The condition has been present for three to twelve months; reported lesion symptoms include itching; self-categorized by the patient as a rash; no associated systemic symptoms reported; the photo was captured at an angle; located on the arm: 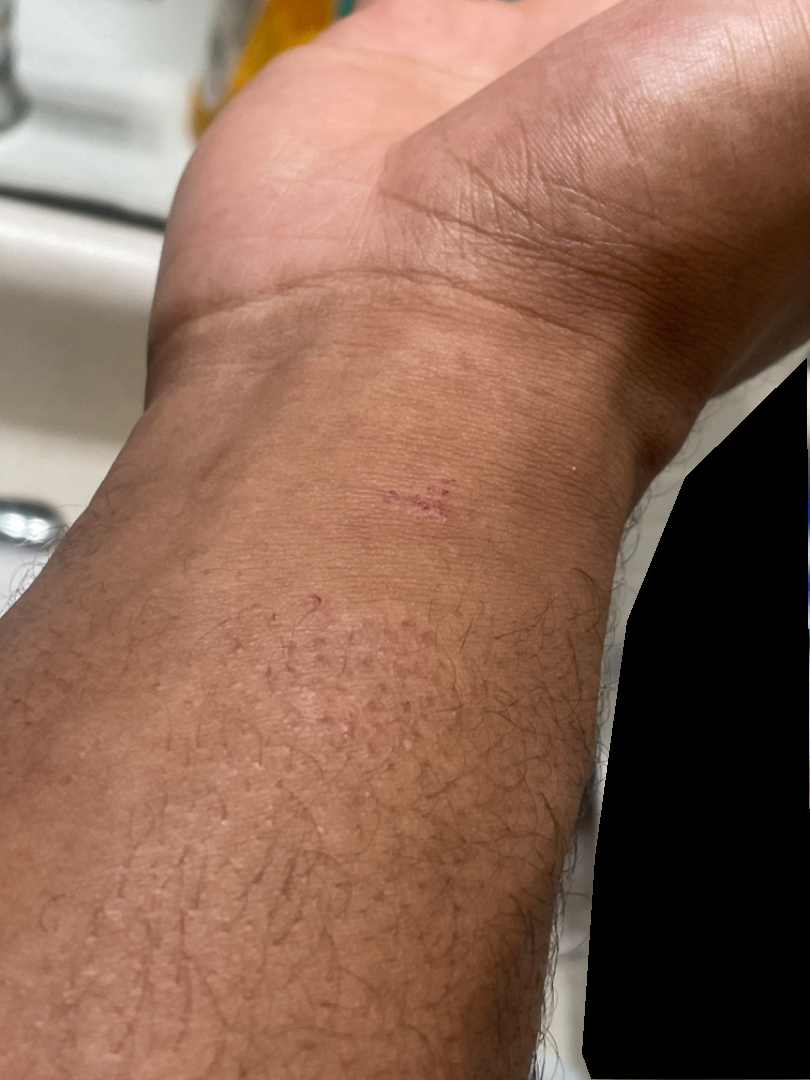Assessment: On dermatologist assessment of the image: the favored diagnosis is Eczema; also consider Impetigo; possibly Allergic Contact Dermatitis.